A dermoscopy image of a single skin lesion · the chart documents a prior melanoma · a female subject aged 68 to 72: 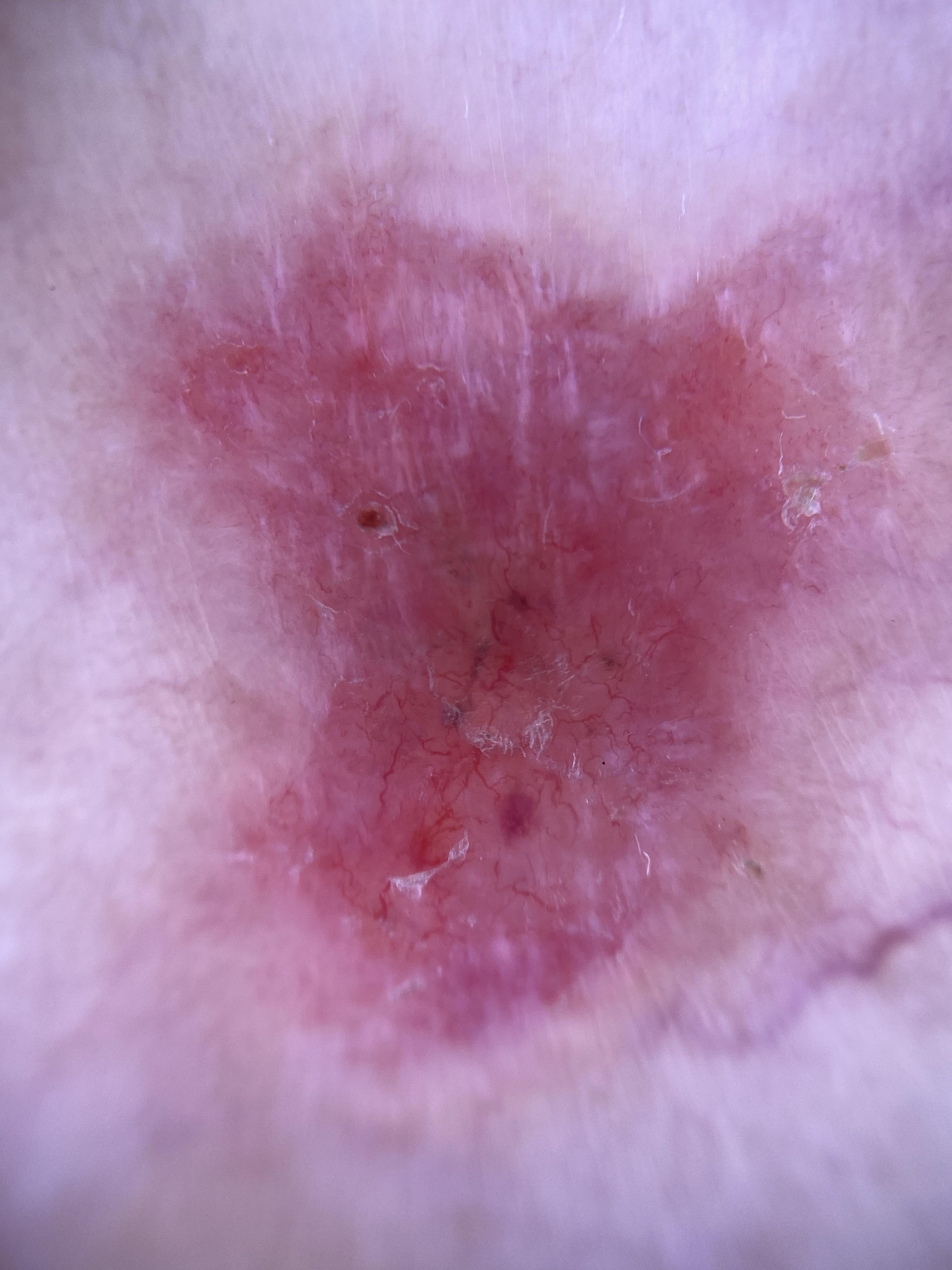Image and clinical context:
The lesion was found on a lower extremity.
Pathology:
The biopsy diagnosis was a basal cell carcinoma.